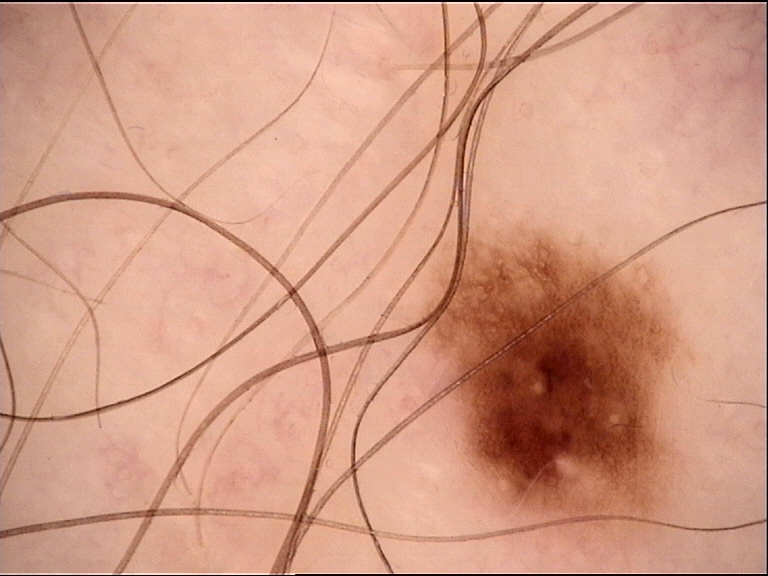Impression: Consistent with a dysplastic junctional nevus.